A dermatoscopic image of a skin lesion.
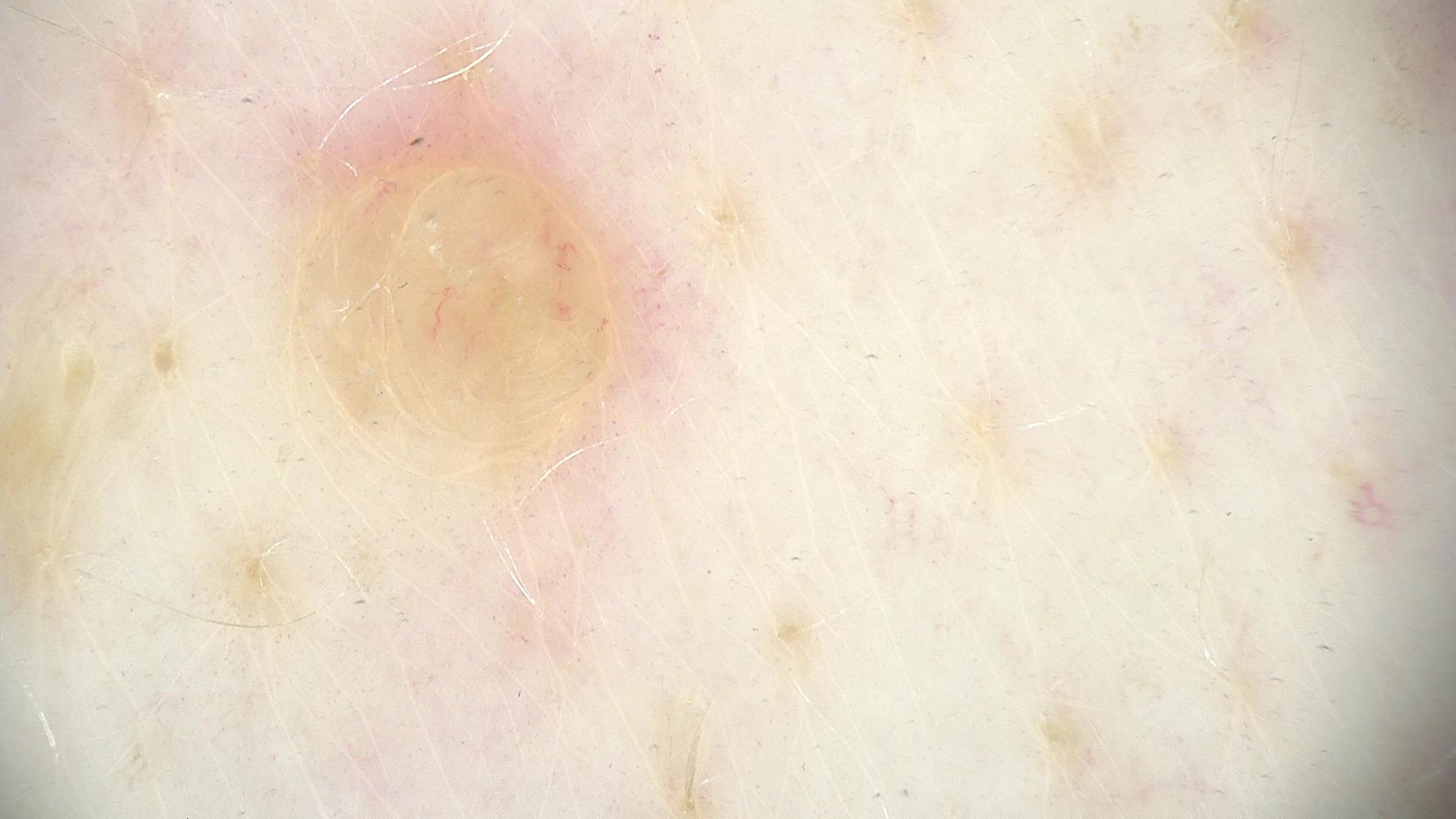<lesion>
<lesion_type>
<main_class>banal</main_class>
<pattern>dermal</pattern>
</lesion_type>
<diagnosis>
<name>dermal nevus</name>
<code>db</code>
<malignancy>benign</malignancy>
<super_class>melanocytic</super_class>
<confirmation>expert consensus</confirmation>
</diagnosis>
</lesion>